A dermoscopic image of a skin lesion:
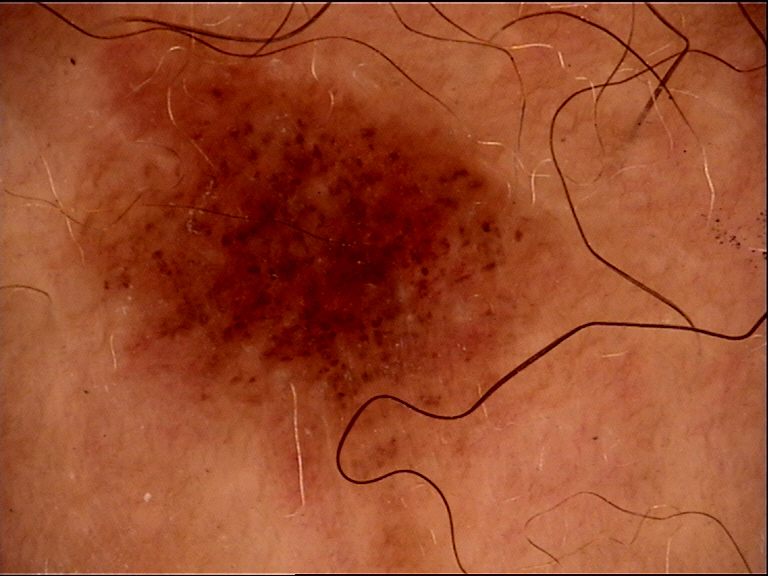Consistent with a dysplastic junctional nevus.